A male patient approximately 40 years of age · a dermoscopic view of a skin lesion:
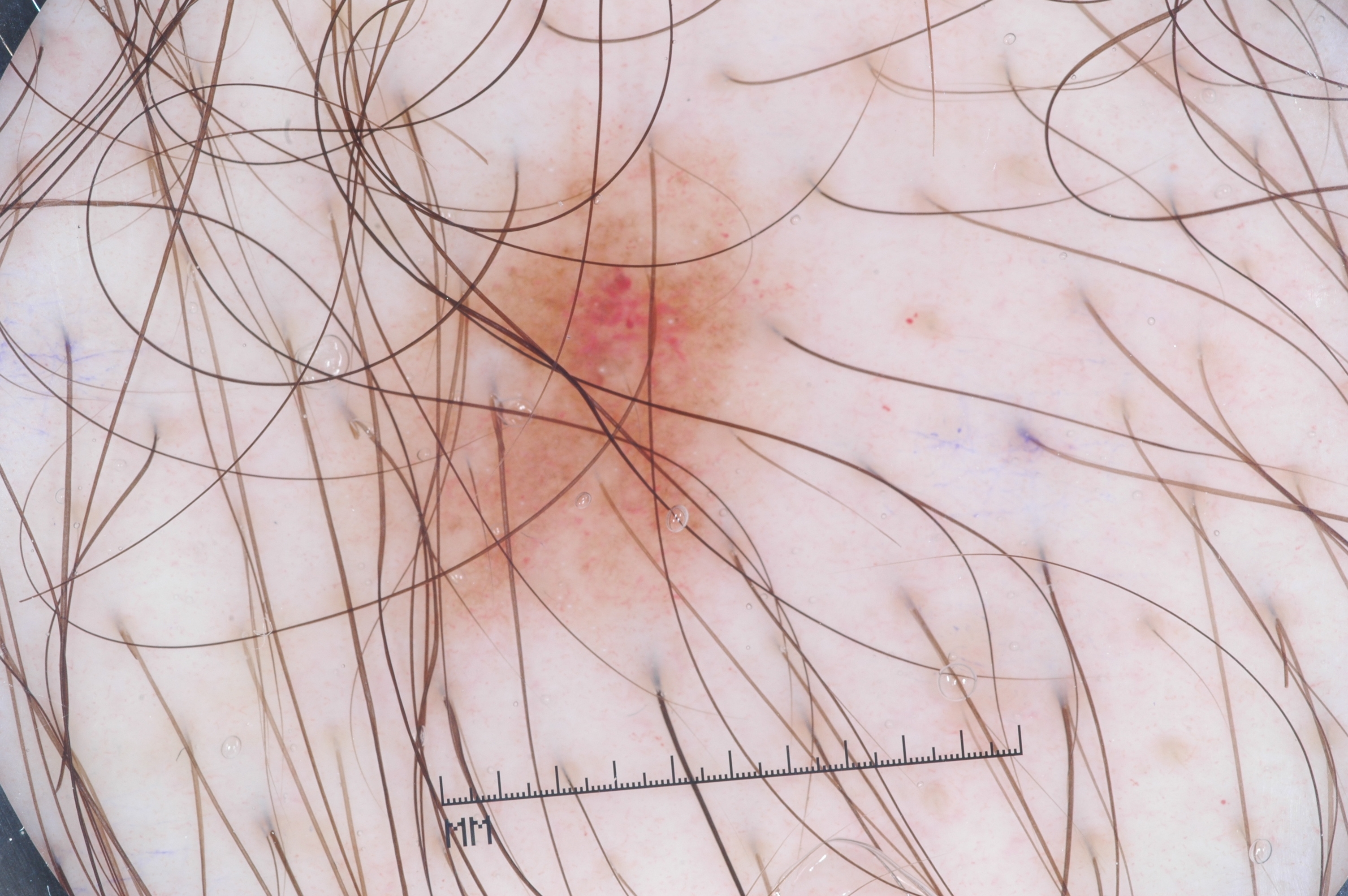Findings:
• features · milia-like cysts; absent: streaks, pigment network, and negative network
• lesion location · 369/140/758/609
• lesion size · moderate
• assessment · a melanocytic nevus